The patient is Fitzpatrick skin type II · a female subject age 73 · a clinical photograph of a skin lesion · the chart records prior skin cancer (patient or family), no tobacco use, and no pesticide exposure.
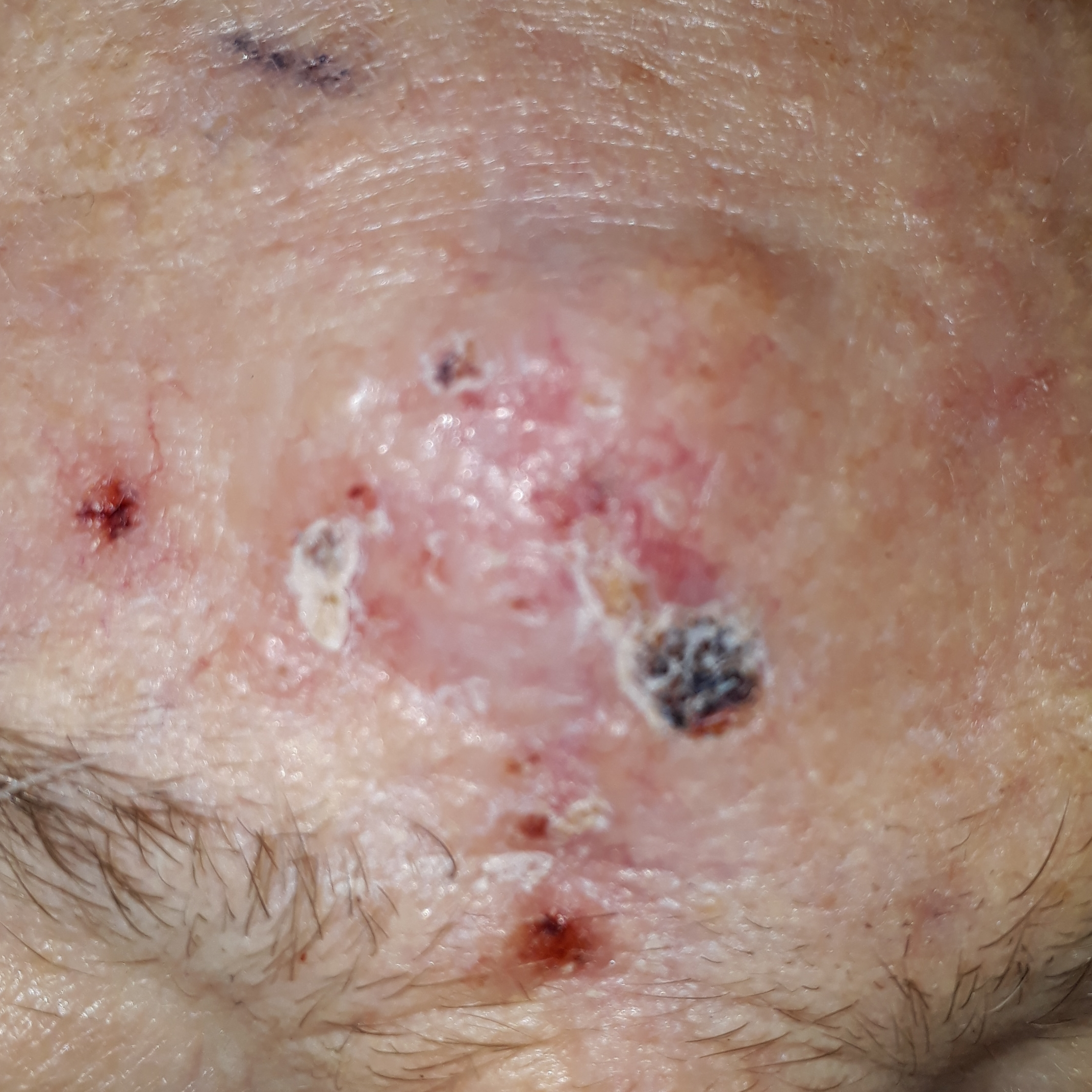Case summary: The lesion is on the face. The lesion measures 25 × 20 mm. The patient reports that the lesion hurts, has bled, is elevated, and itches. Conclusion: Histopathologically confirmed as a basal cell carcinoma.